Present for less than one week. Skin tone: Fitzpatrick I; non-clinician graders estimated 2 on the MST. Located on the leg. No associated systemic symptoms reported. The photograph is a close-up of the affected area. Texture is reported as rough or flaky, raised or bumpy and flat. The patient considered this a rash:
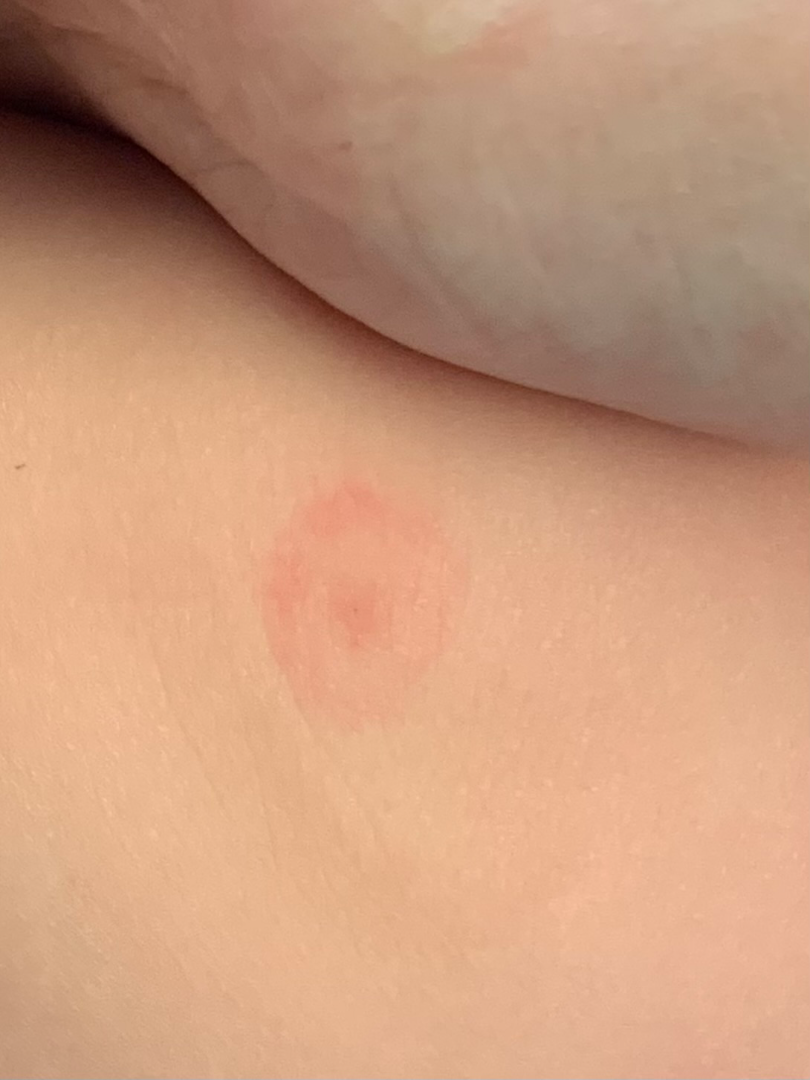Q: What conditions are considered?
A: the differential is split between Insect Bite, Geographic tongue and Contact dermatitis